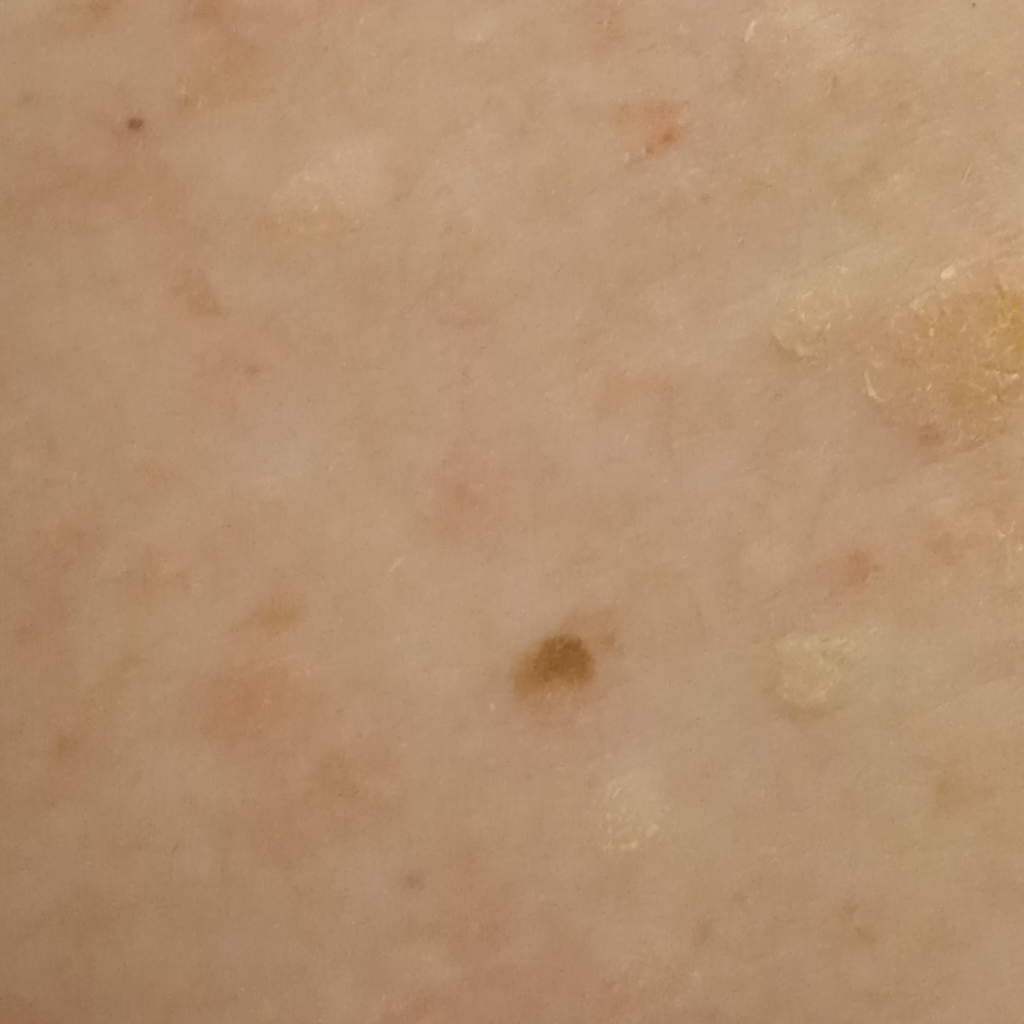The patient reports a personal history of skin cancer and a personal history of cancer.
A moderate number of moles by the patient's own estimate.
Imaged for a research study, with no referral diagnosis recorded.
A macroscopic clinical photograph of a skin lesion.
A male subject aged 77.
The patient says their skin reddens with sun exposure.
The lesion involves the back.
Measuring roughly 3 mm.
The diagnostic impression was a seborrheic keratosis.